Dermoscopy of a skin lesion · the patient is a male approximately 40 years of age.
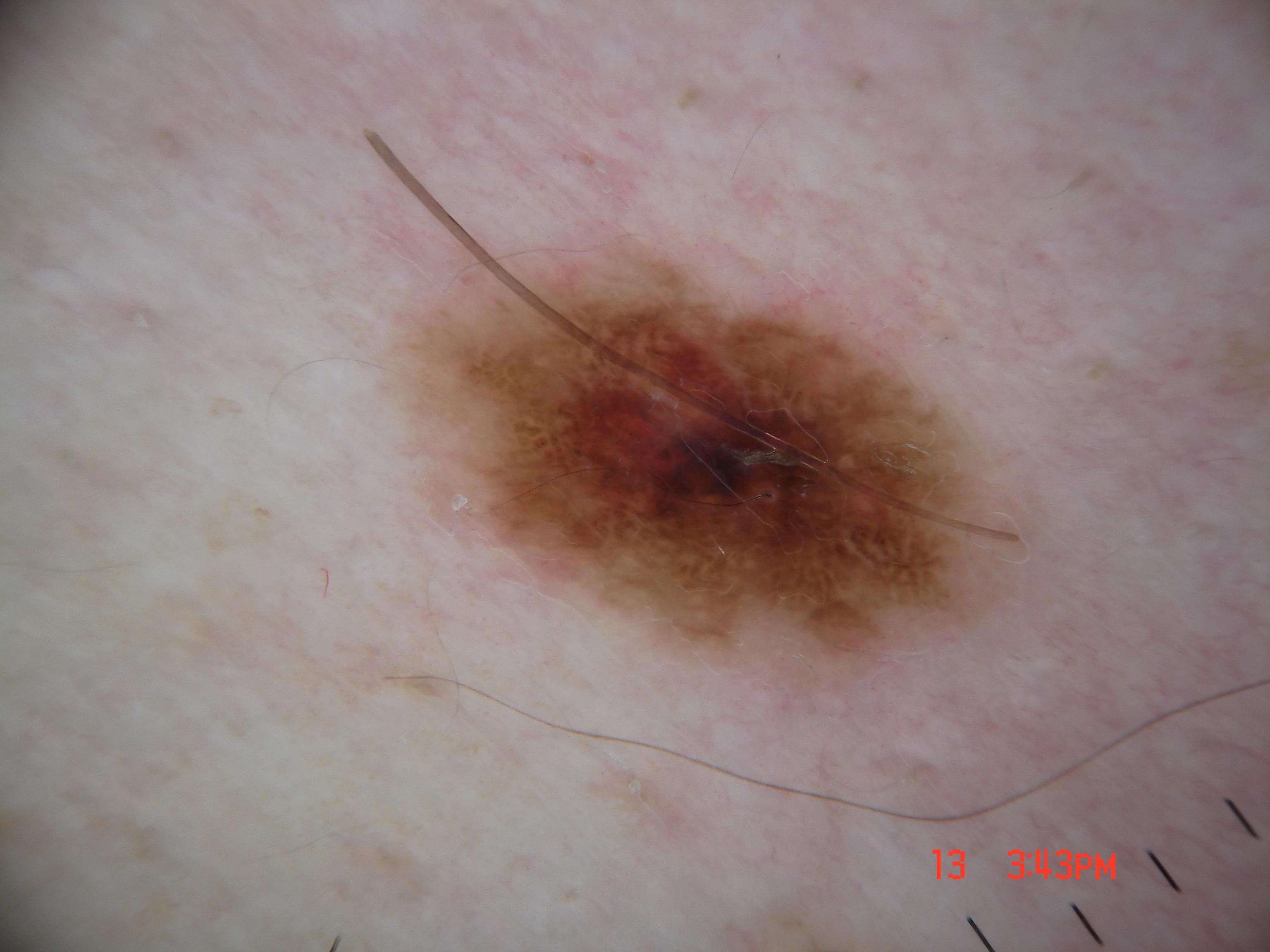Findings:
– extent — ~16% of the field
– dermoscopic findings — globules and negative network; absent: milia-like cysts, streaks, and pigment network
– lesion location — [386,236,1035,686]
– diagnosis — a melanoma